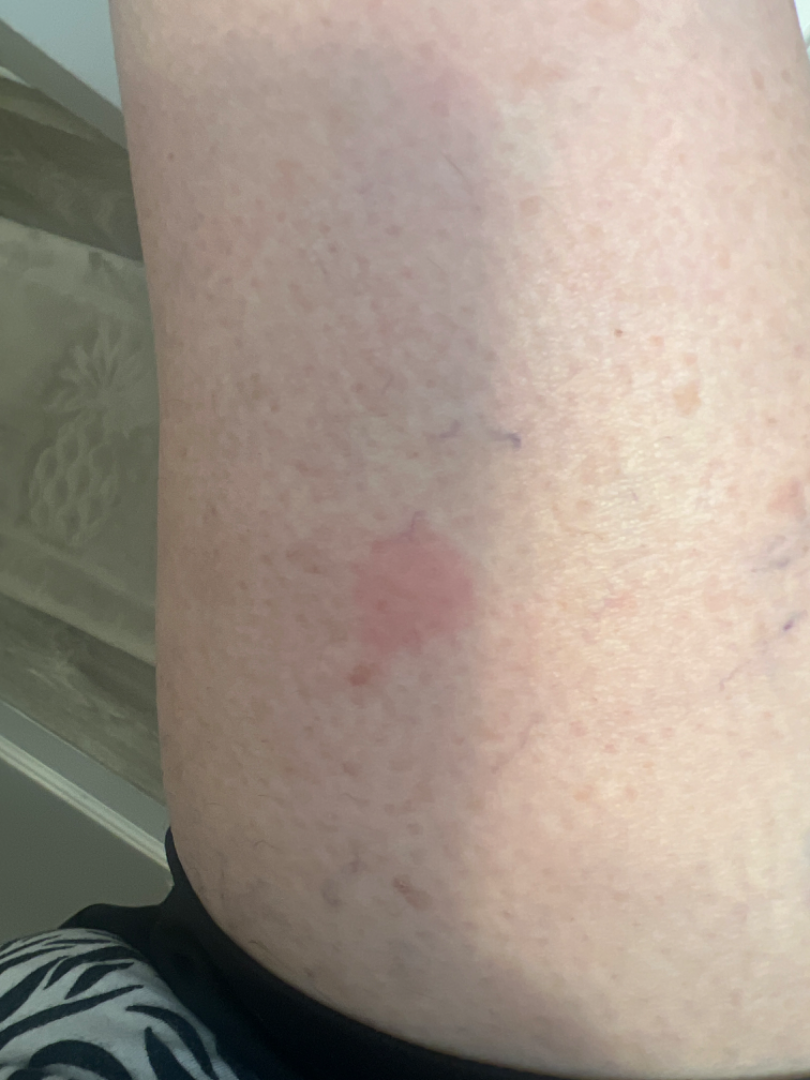photo taken=at an angle | location=leg and arm | differential diagnosis=one reviewing dermatologist: in keeping with Insect Bite.